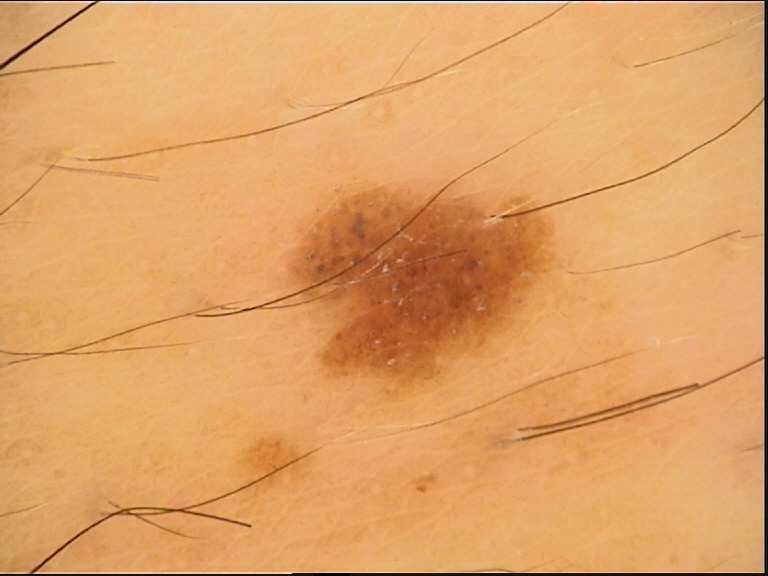Case:
A dermoscopic photograph of a skin lesion.
Conclusion:
Labeled as a benign lesion — a dysplastic compound nevus.